Dermoscopy of a skin lesion:
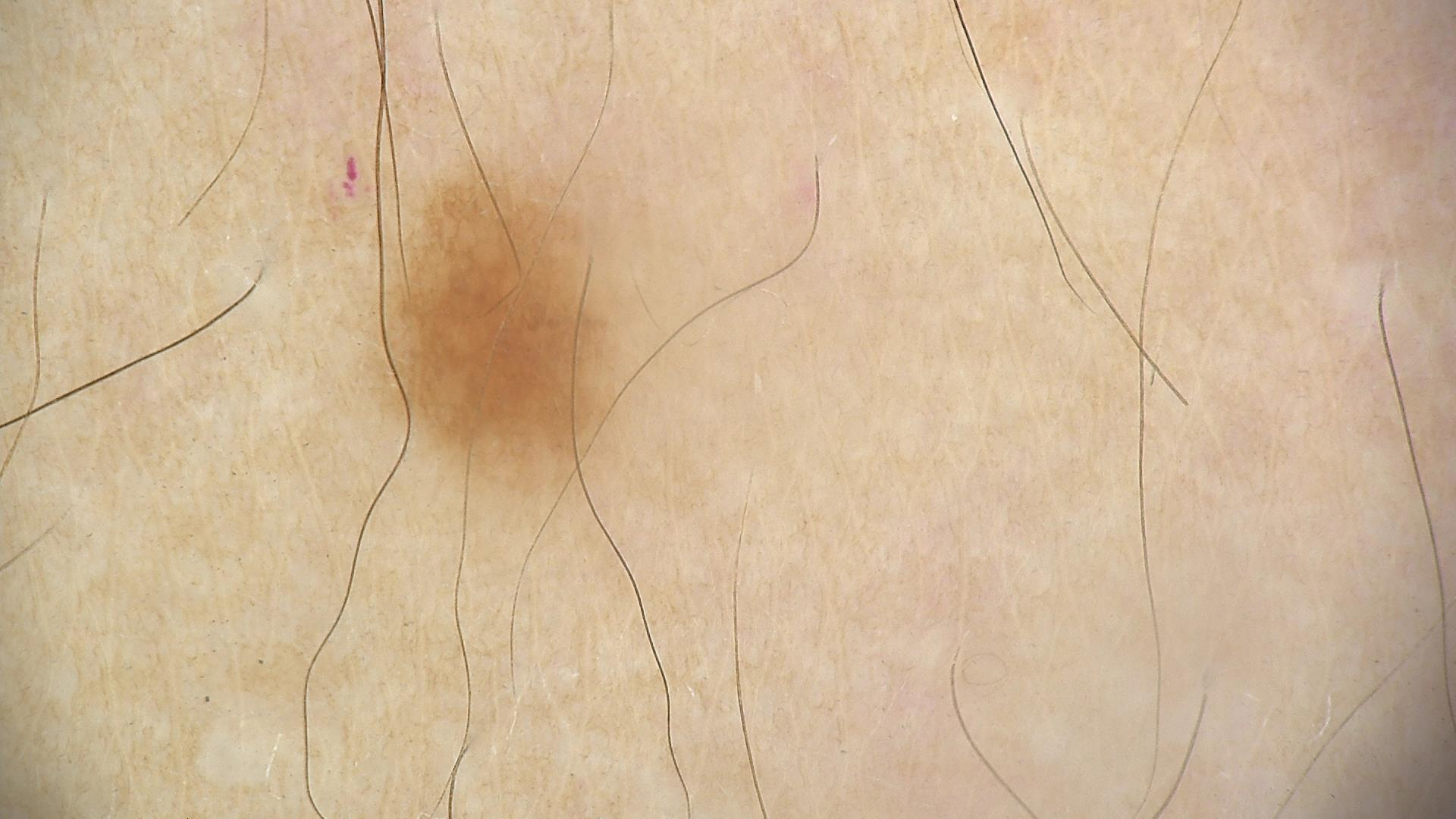diagnostic label=dysplastic junctional nevus (expert consensus)